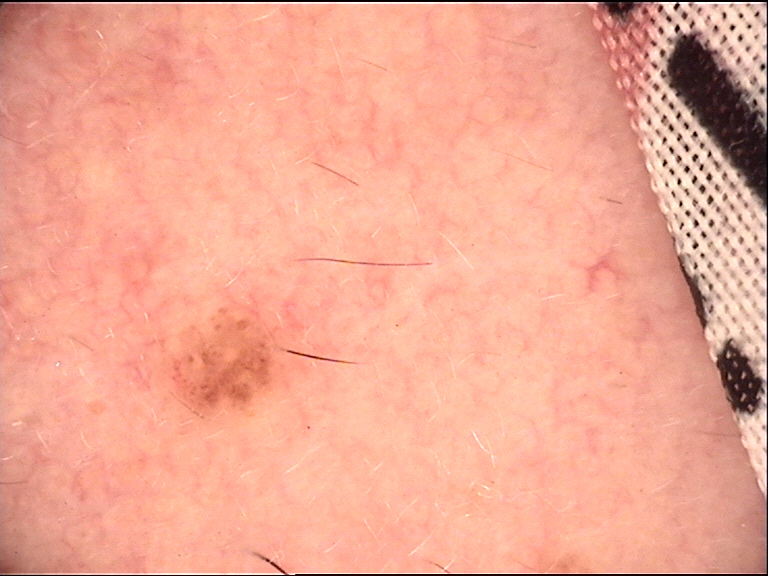This is a banal lesion. The diagnostic label was a dermal nevus.